The leg is involved; this is a close-up image — 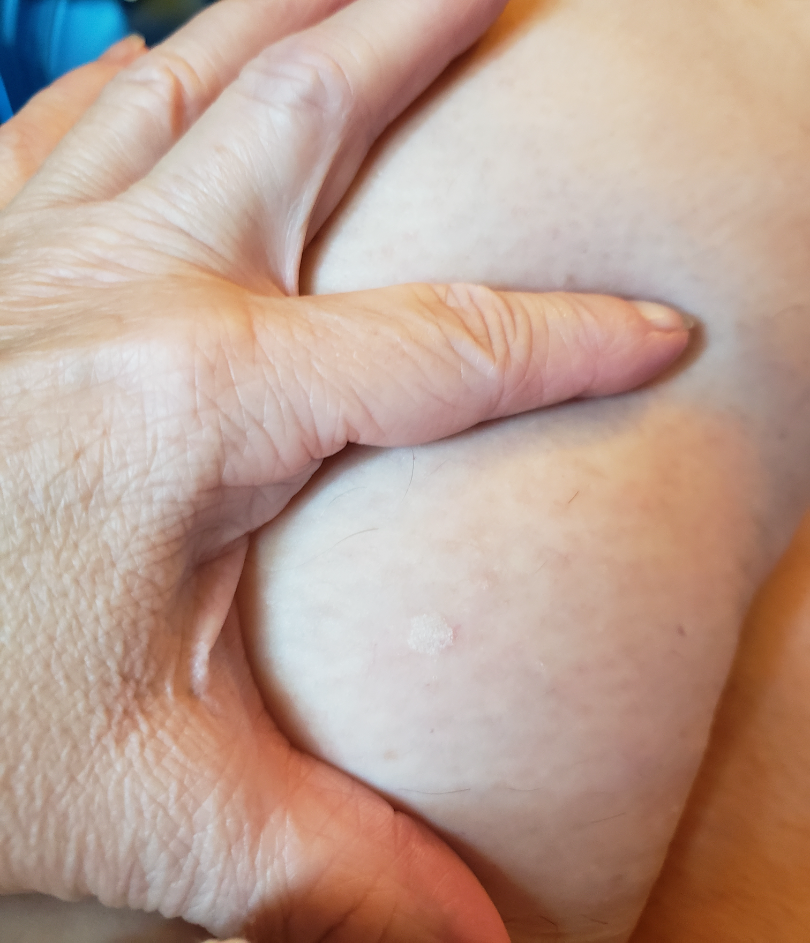<report>
  <differential>Verruca vulgaris, SK/ISK</differential>
</report>